Dermoscopy of a skin lesion: 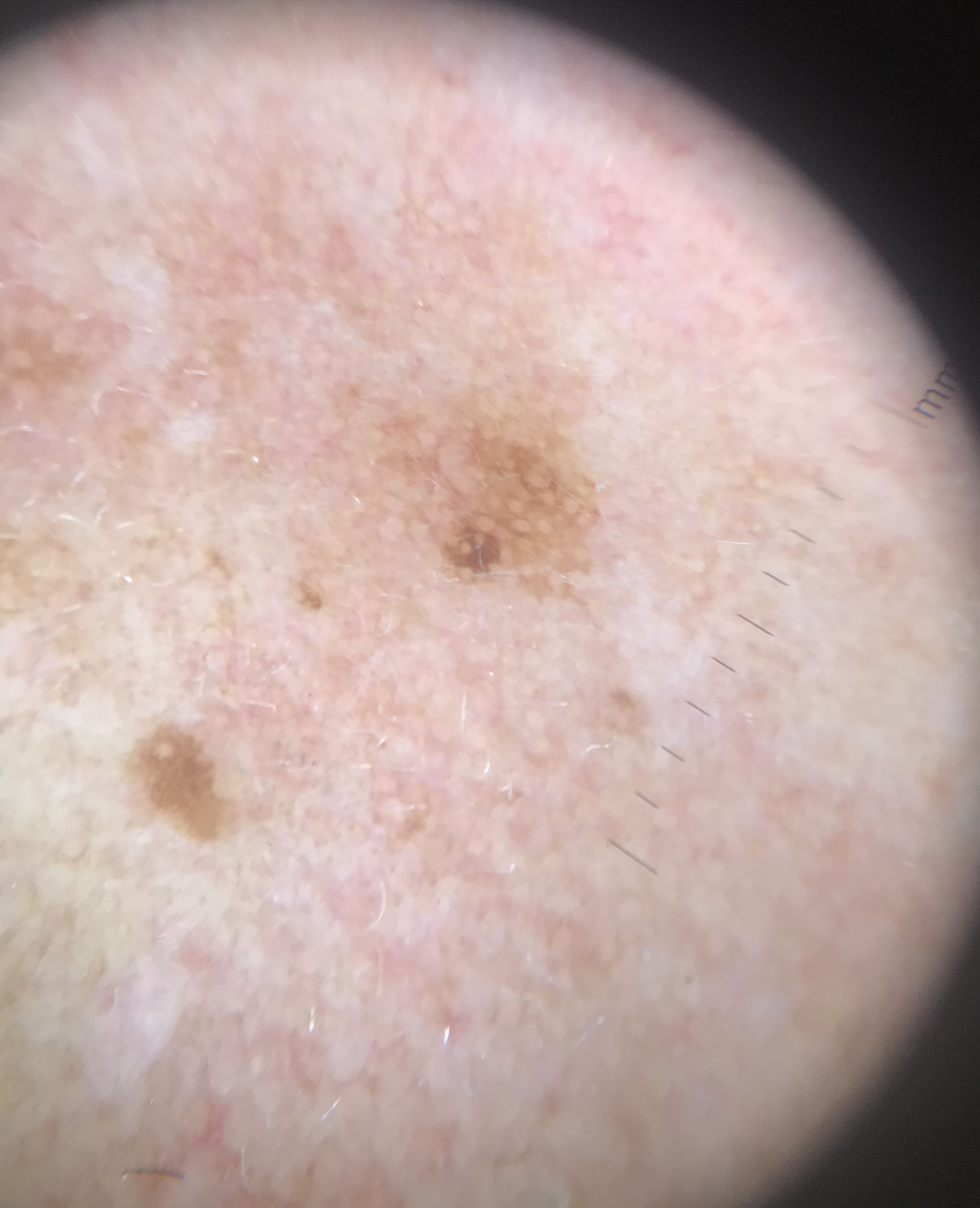subtype — keratinocytic; diagnostic label — seborrheic keratosis (expert consensus).